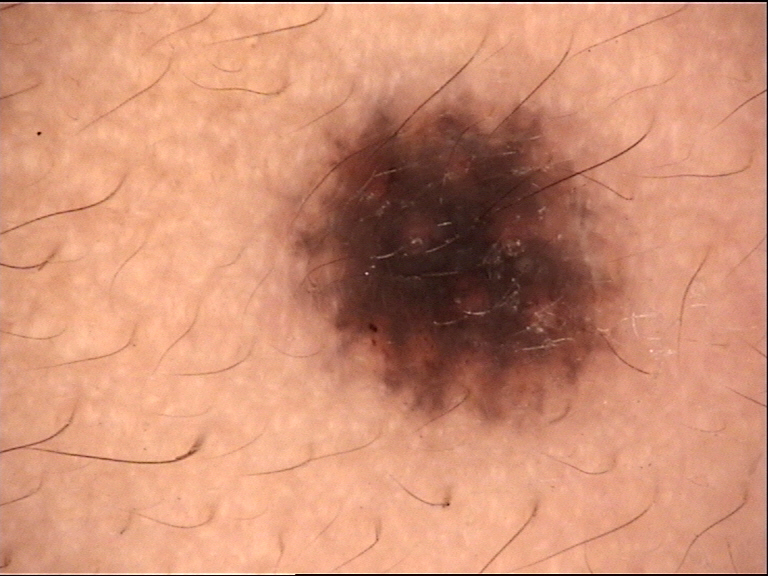* imaging · dermatoscopy
* class · compound nevus (expert consensus)